A skin lesion imaged with a dermatoscope: 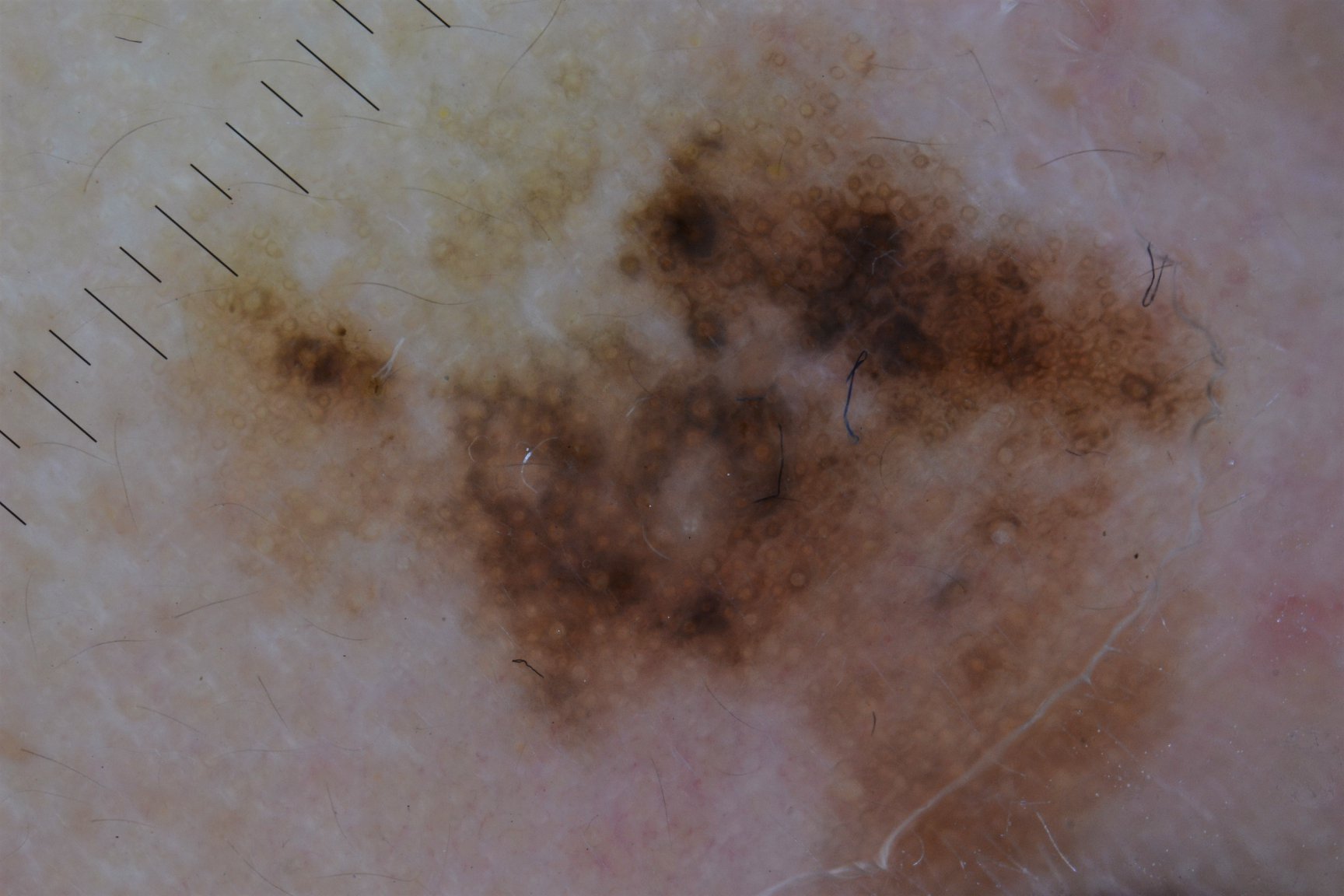diagnosis: lentigo maligna (biopsy-proven).